A dermoscopic view of a skin lesion: 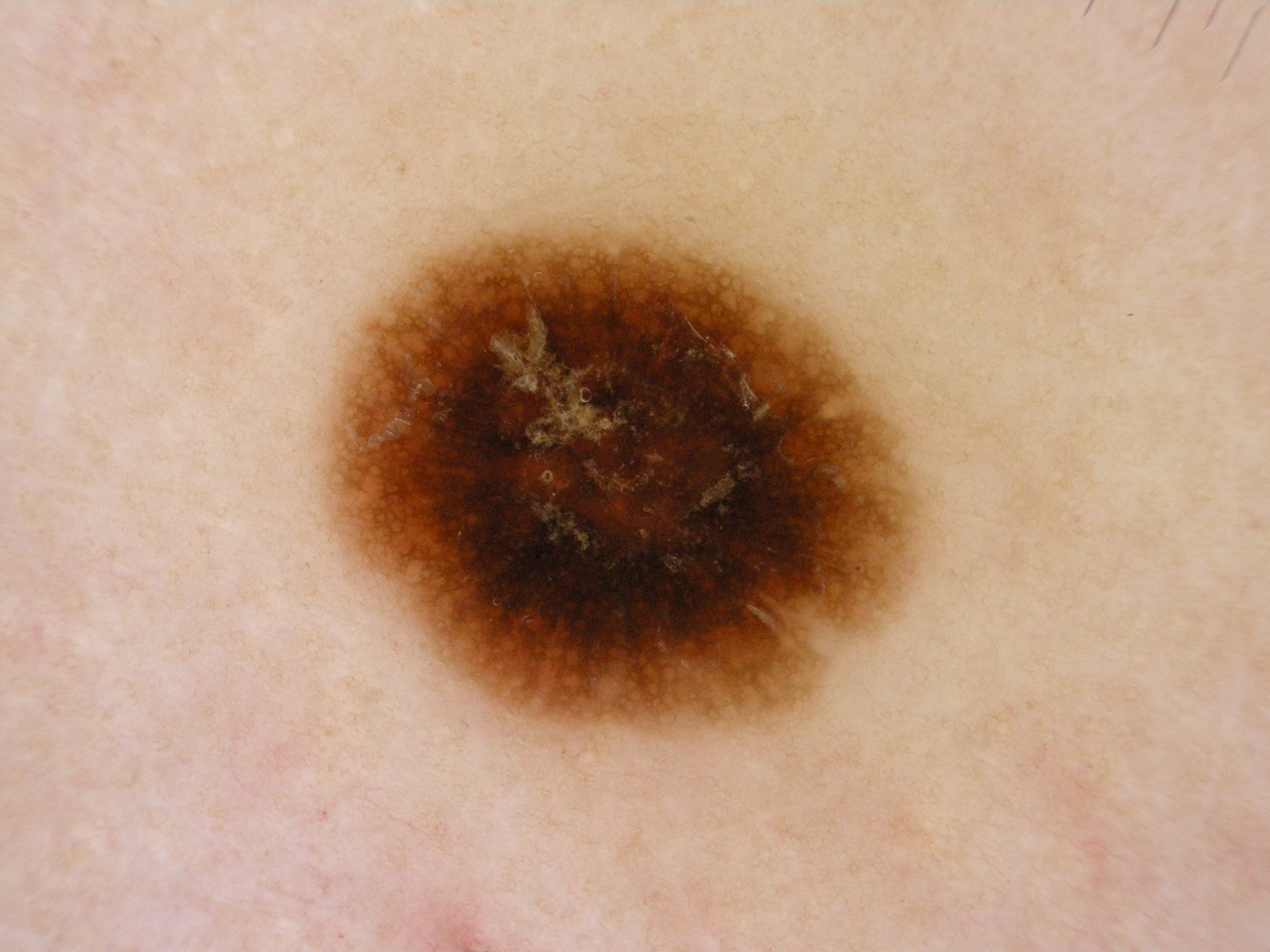The dermoscopic pattern shows pigment network; no globules, negative network, milia-like cysts, or streaks.
The lesion's extent is 332, 226, 921, 733.
Clinically diagnosed as a melanocytic nevus.